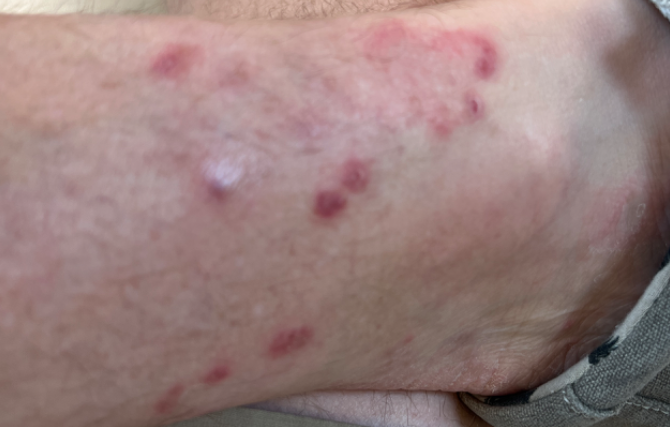{
  "duration": "three to twelve months",
  "skin_tone": {
    "fitzpatrick": "I"
  },
  "shot_type": "at an angle",
  "patient_category": "a rash",
  "differential": {
    "Tinea": 0.54,
    "Granuloma annulare": 0.23,
    "Eczema": 0.23
  }
}